The photo was captured at an angle, Fitzpatrick skin type III; lay reviewers estimated Monk skin tone scale 1 or 2 (two reviewer pools) — 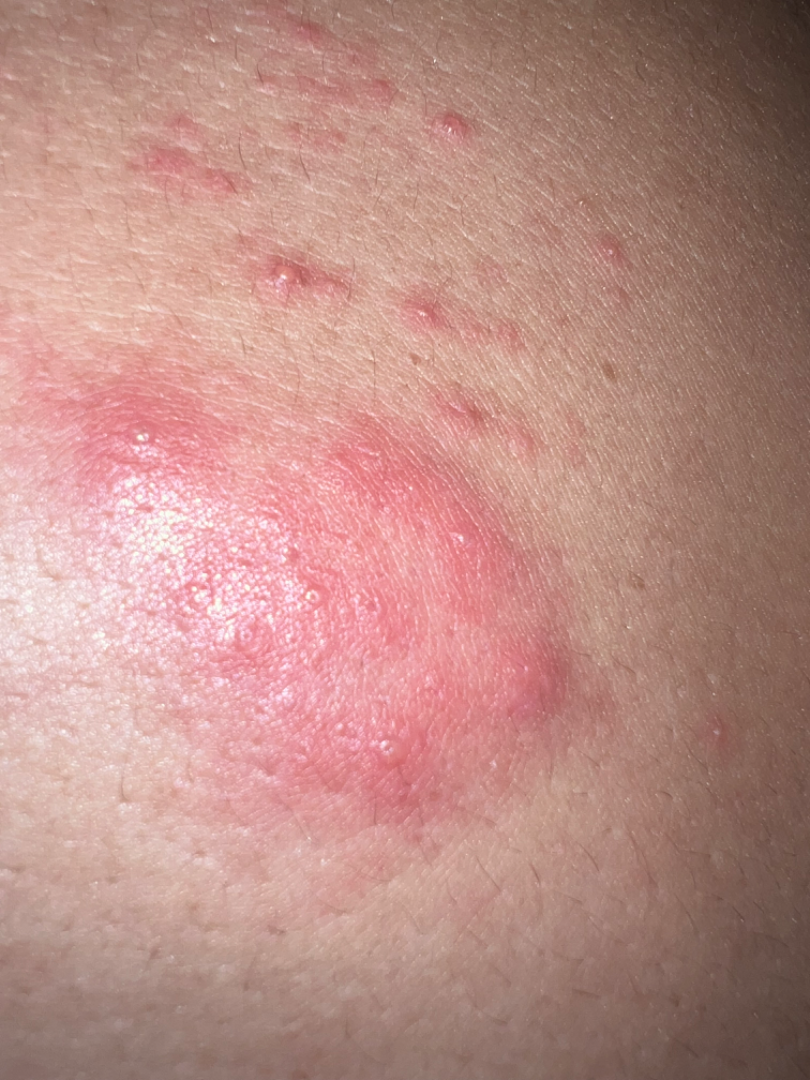Notes:
• differential diagnosis · the primary impression is Herpes Zoster; also raised was Allergic Contact Dermatitis